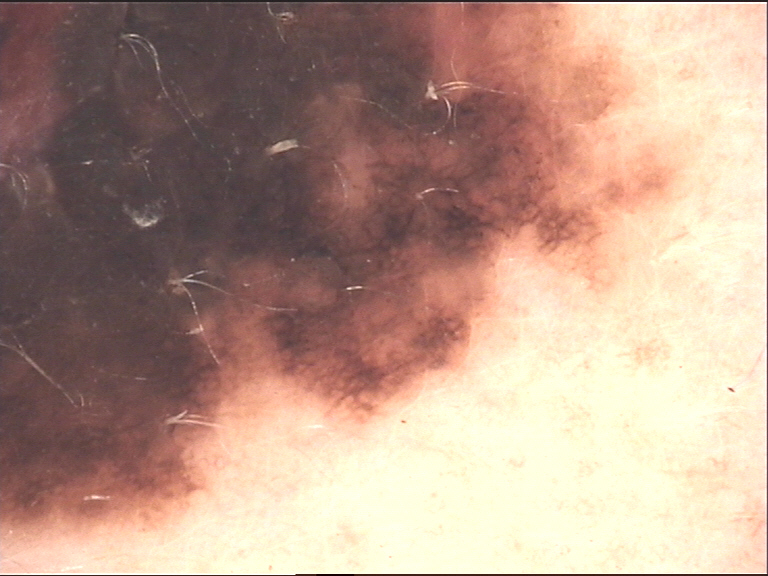Biopsy-confirmed as a melanoma.